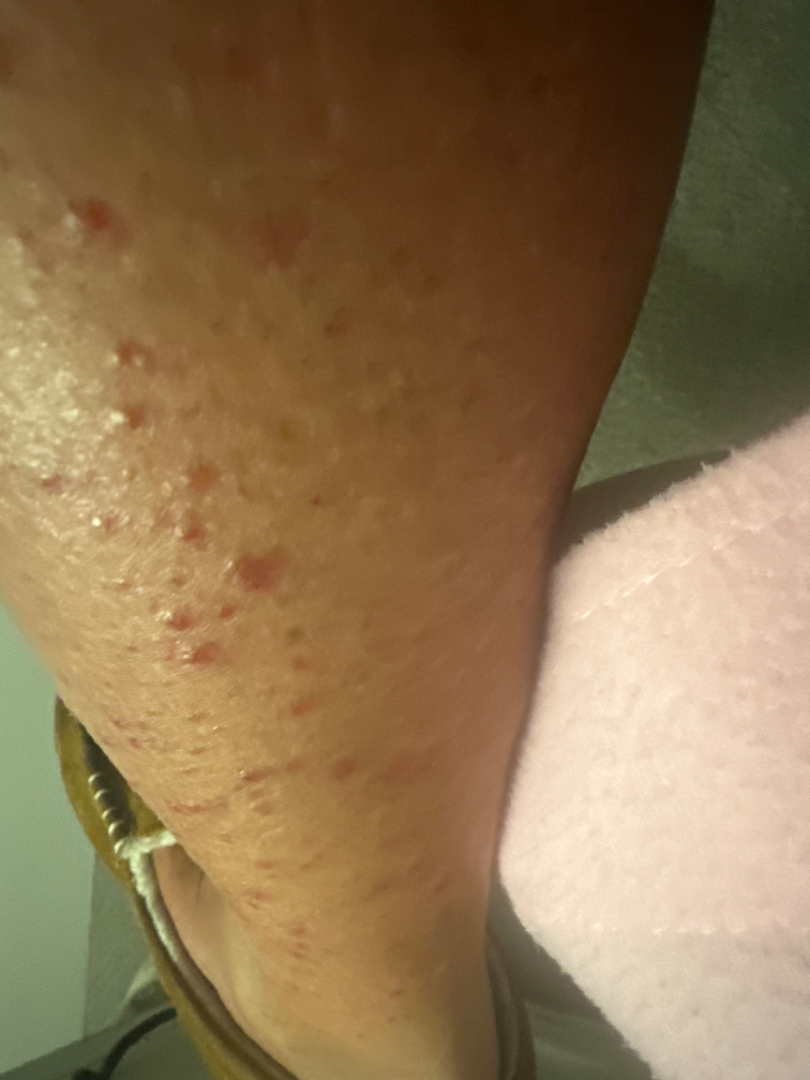| key | value |
|---|---|
| shot type | at an angle |
| subject | female, age 50–59 |
| site | arm and leg |
| differential | Hypersensitivity (most likely); Lichen planus/lichenoid eruption (considered) |